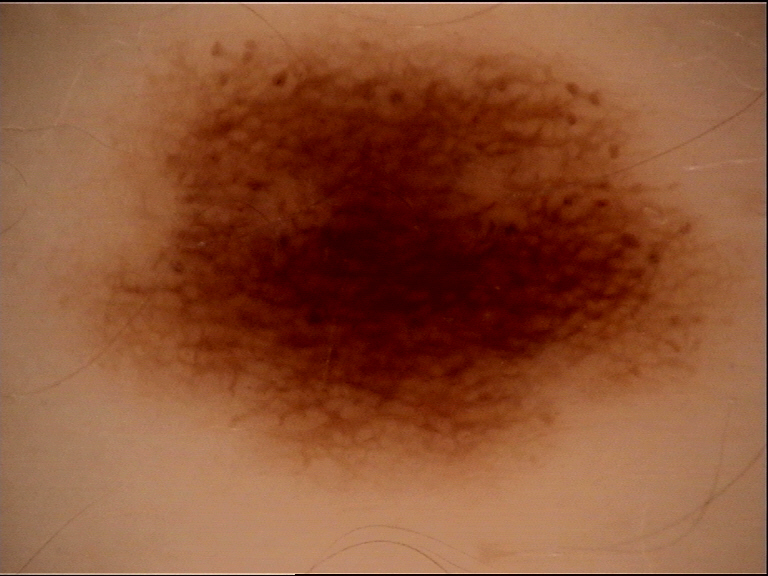assessment=dysplastic junctional nevus (expert consensus)